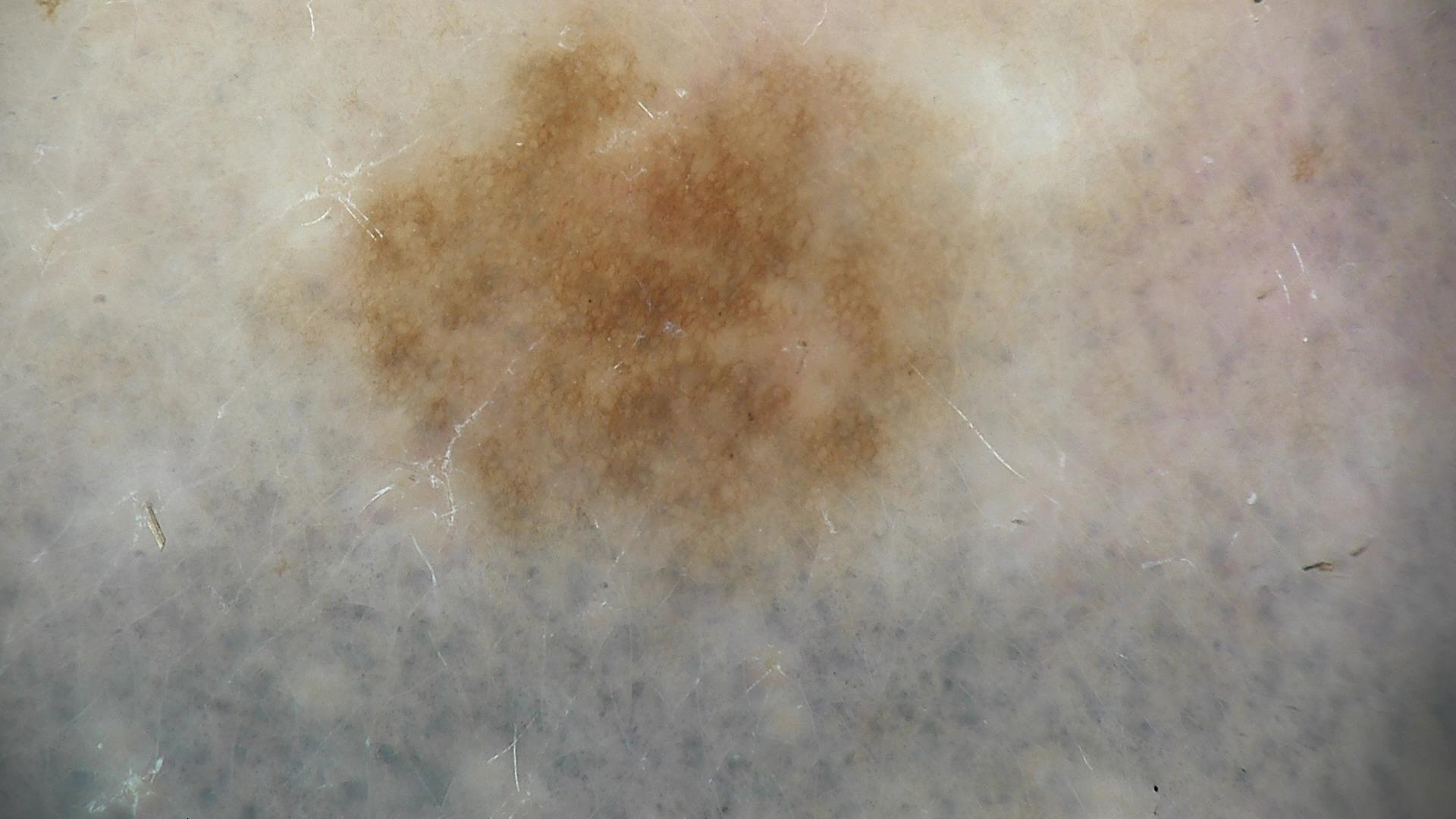A skin lesion imaged with a dermatoscope.
Labeled as a dysplastic junctional nevus.